Recorded as Fitzpatrick III; a female subject aged around 30; a contact-polarized dermoscopy image of a skin lesion.
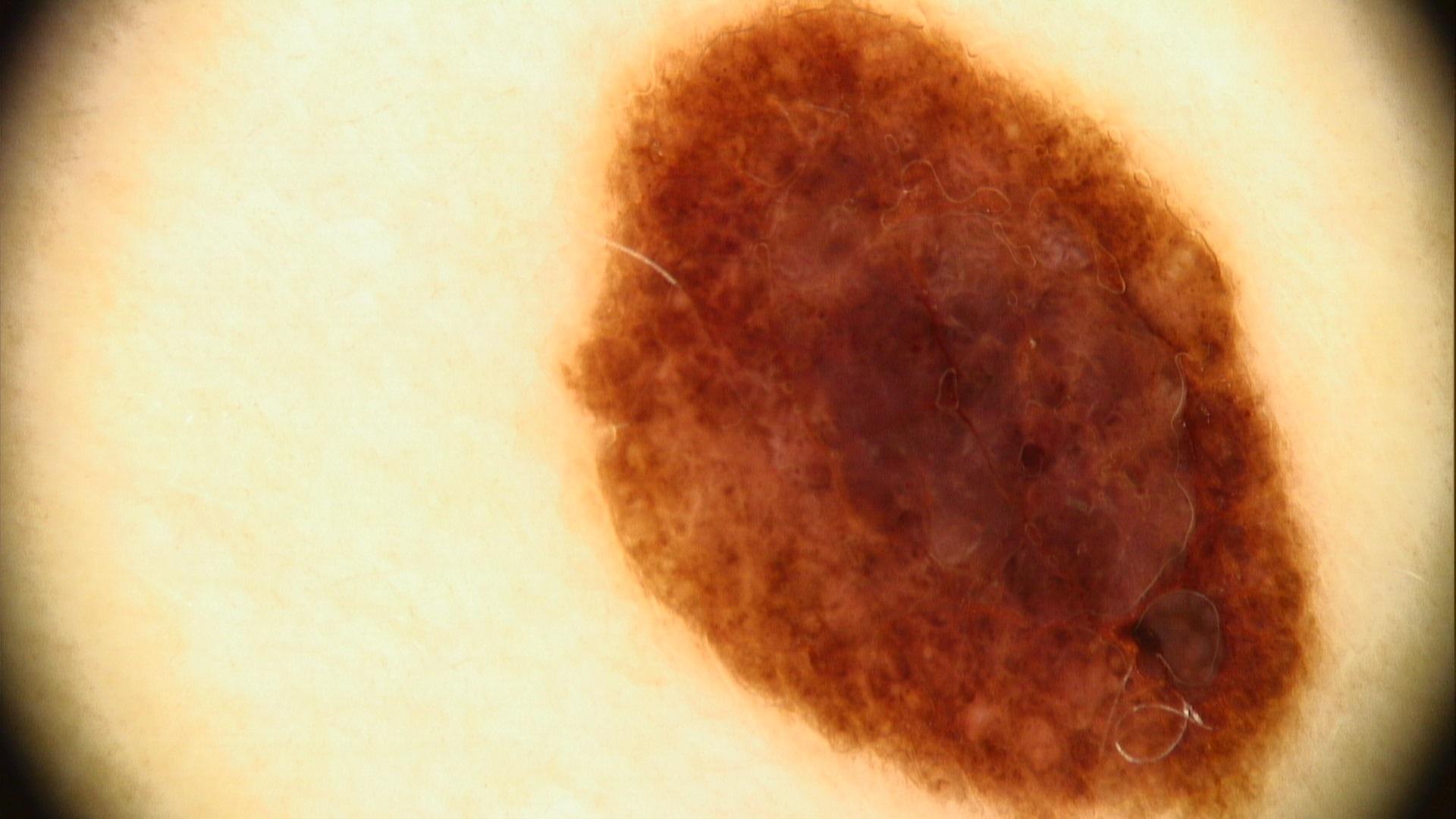site — the trunk; diagnostic label — Nevus (clinical impression).